A skin lesion imaged with a dermatoscope: 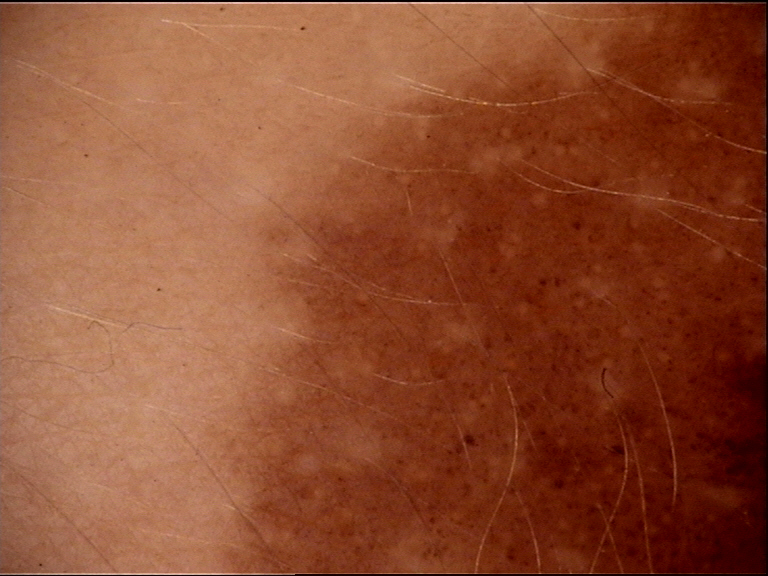category=banal | diagnostic label=congenital junctional nevus (expert consensus).